The patient describes having a moderate number of moles. Acquired for a research image collection, with no referral diagnosis. A female subject 50 years of age. The patient says their skin reddens painfully with sun exposure. Dermoscopy of a skin lesion: 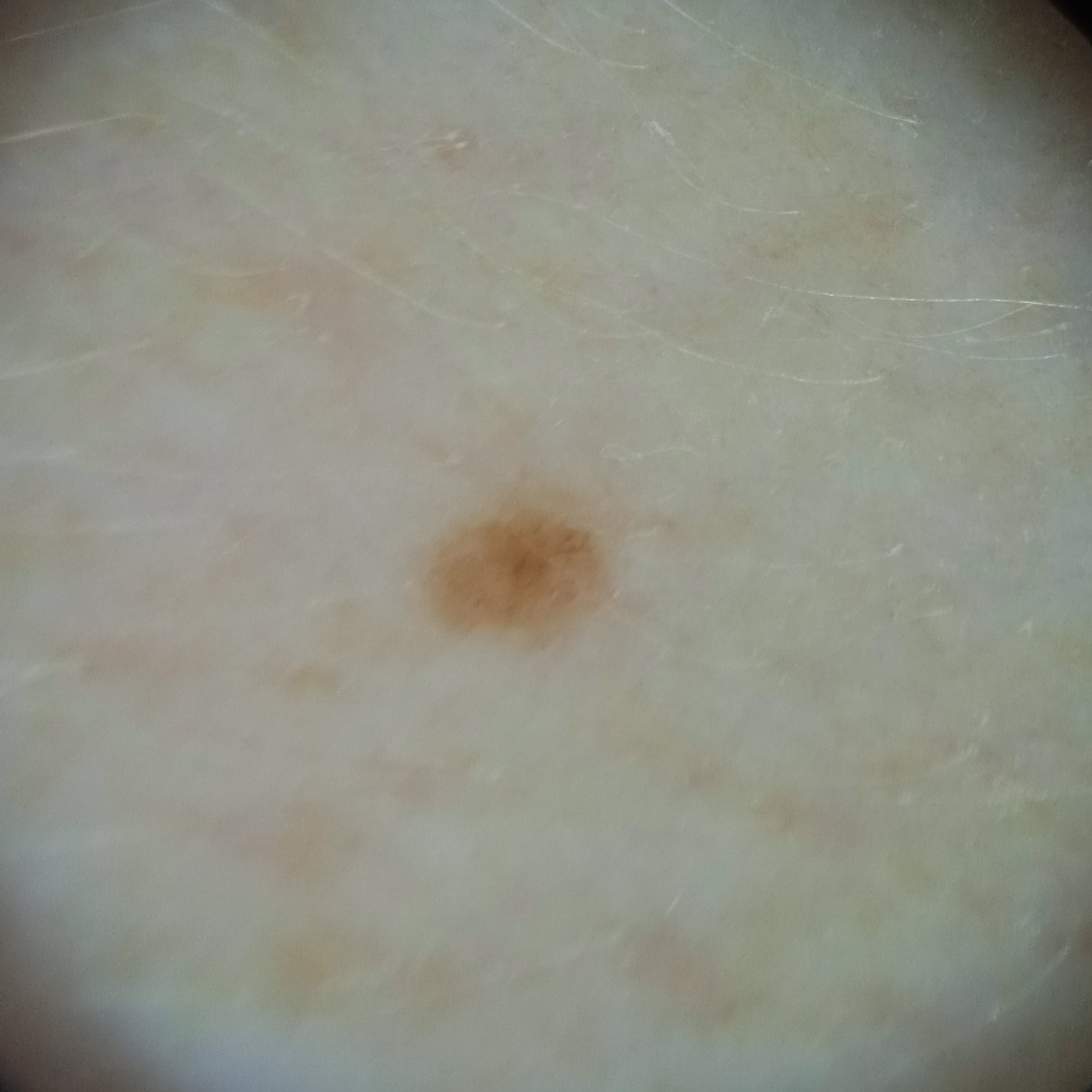Case summary:
Measuring roughly 2 mm.
Conclusion:
The diagnostic impression was a melanocytic nevus.